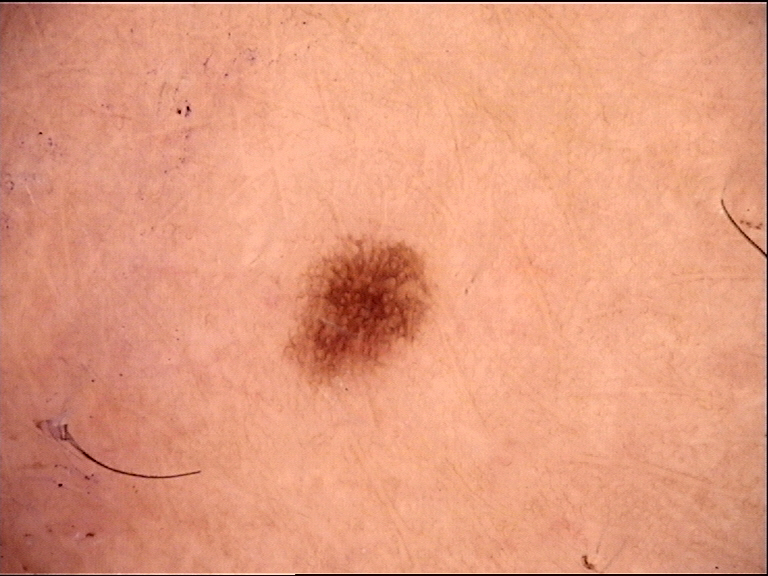Conclusion: Labeled as a junctional nevus.